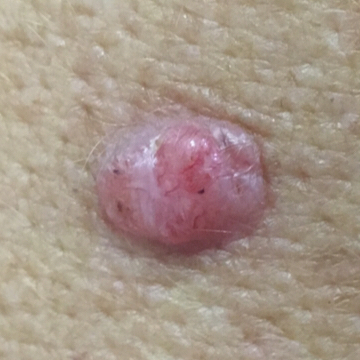Patient and lesion:
FST II. A clinical close-up photograph of a skin lesion. A male subject 53 years old. The lesion is on an arm. The lesion measures 10 × 8 mm. By the patient's account, the lesion has bled, has grown, itches, hurts, and is elevated.
Conclusion:
Histopathology confirmed a basal cell carcinoma.